A dermoscopic photograph of a skin lesion.
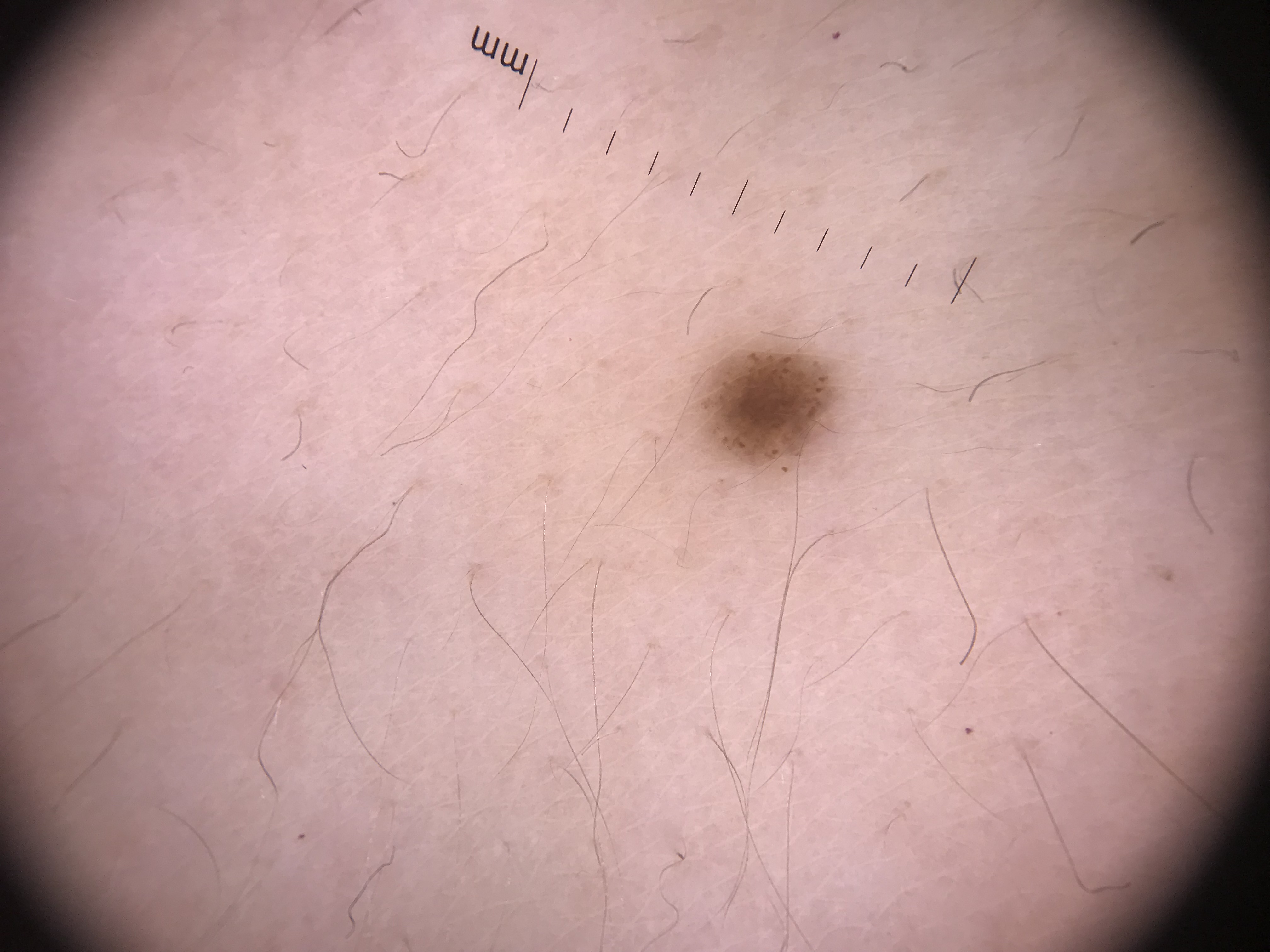- diagnostic label · junctional nevus (expert consensus)